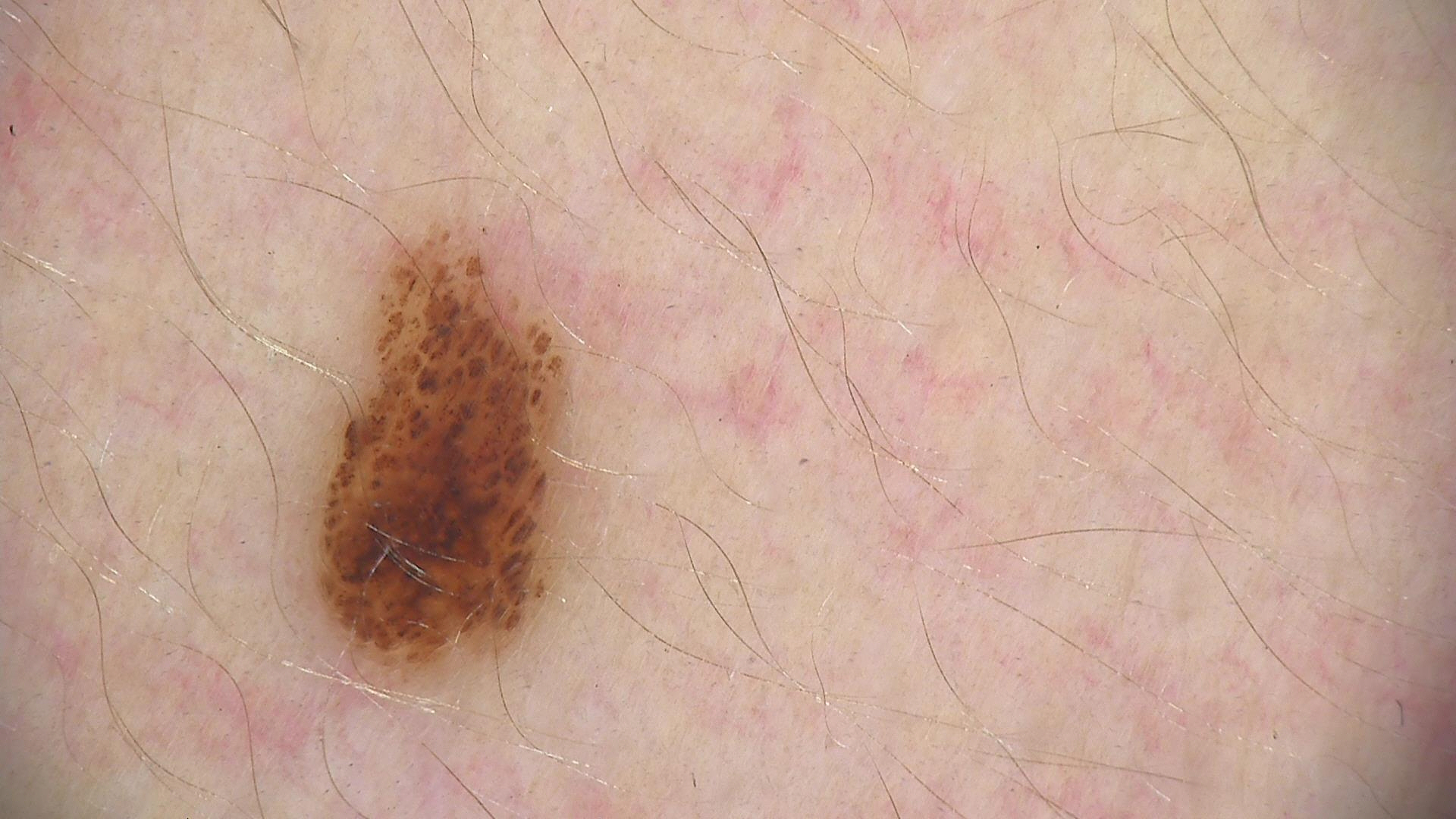label=compound nevus (expert consensus).